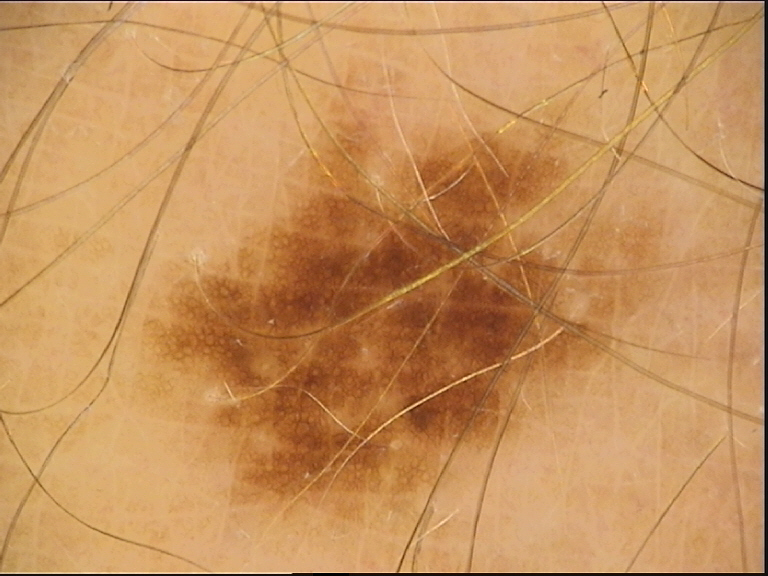<dermoscopy>
  <diagnosis>
    <name>dysplastic junctional nevus</name>
    <code>jd</code>
    <malignancy>benign</malignancy>
    <super_class>melanocytic</super_class>
    <confirmation>expert consensus</confirmation>
  </diagnosis>
</dermoscopy>